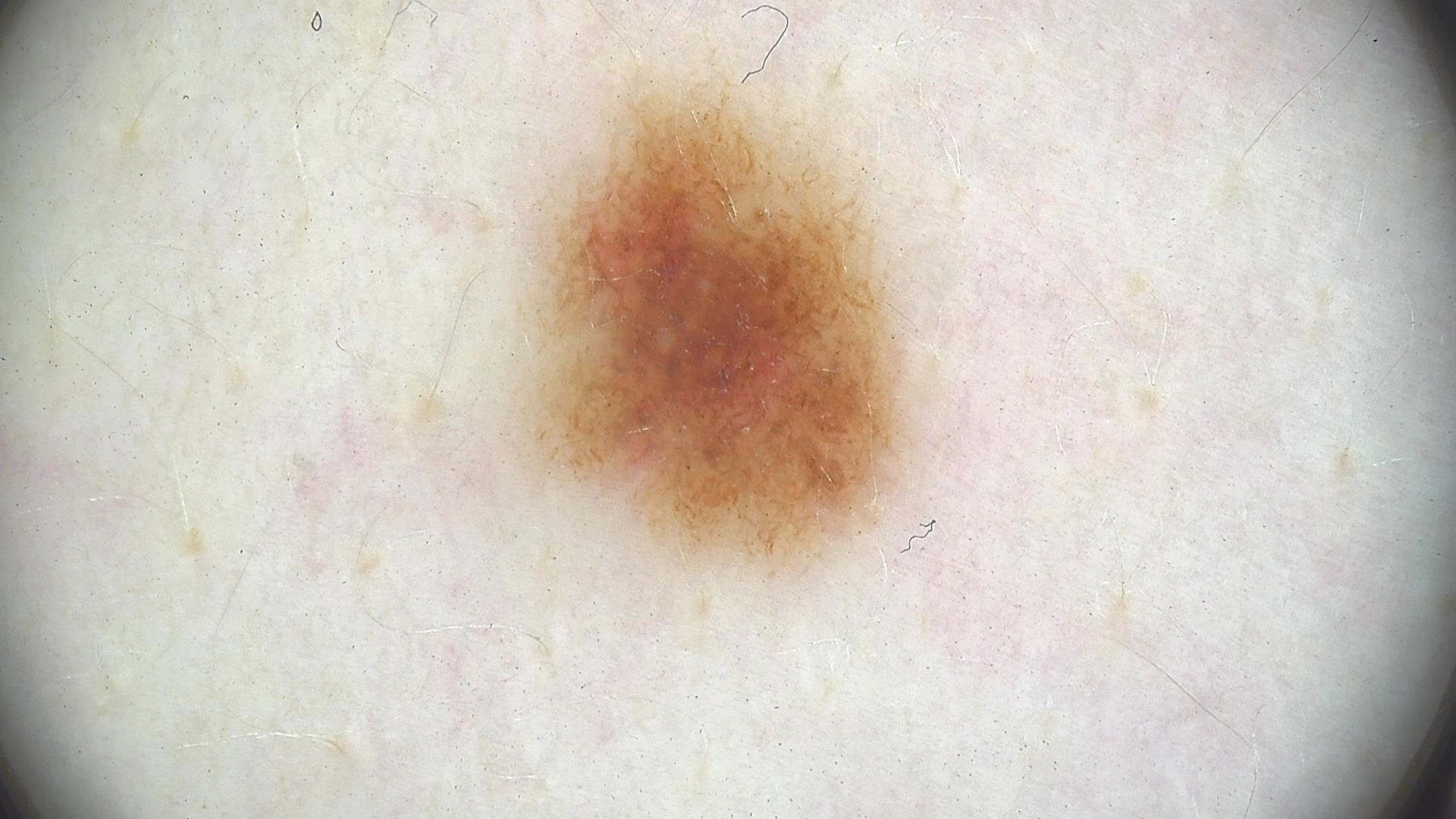diagnosis = dysplastic junctional nevus (expert consensus).